The lesion involves the leg · the photograph was taken at an angle.
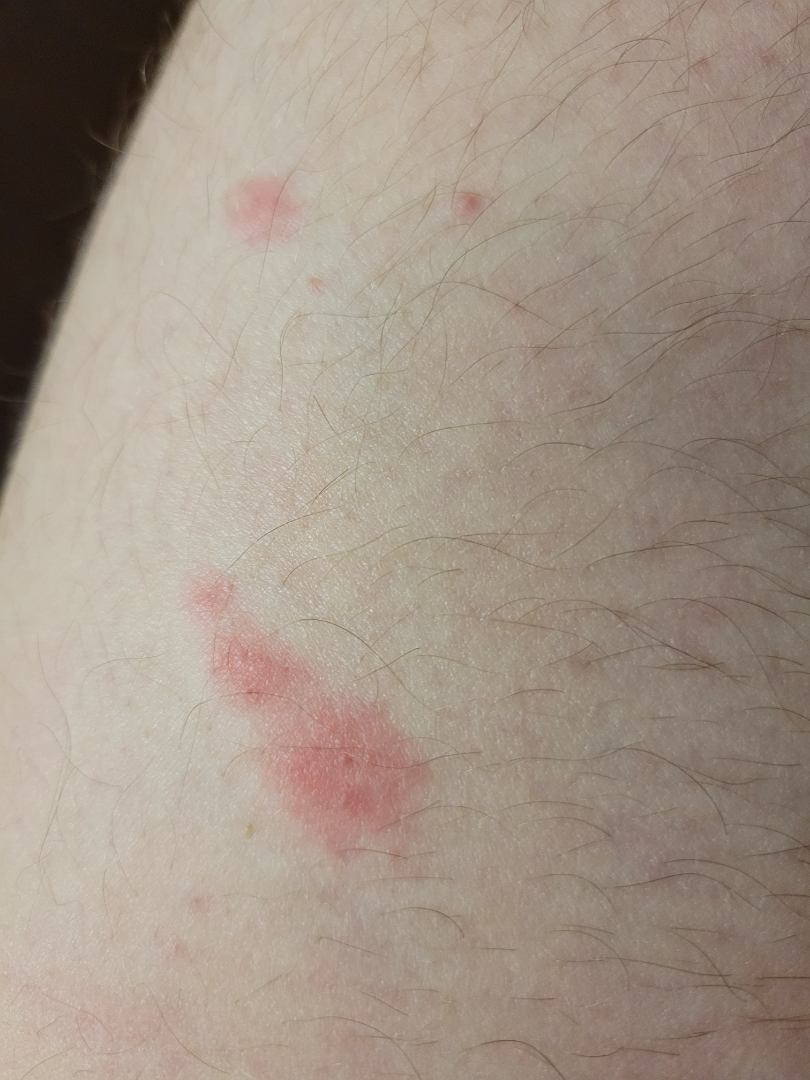The contributor notes the lesion is raised or bumpy.
The contributor notes the condition has been present for about one day.
The patient considered this a rash.
Most likely Insect Bite.